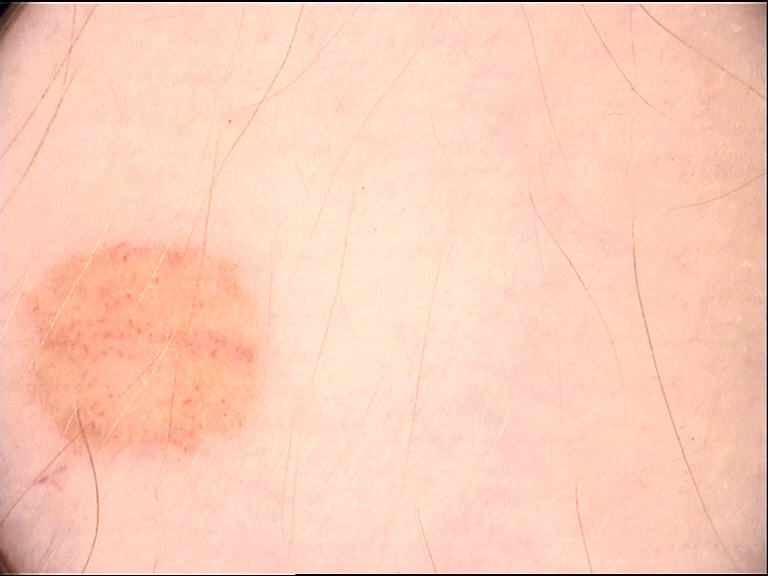image: dermoscopy
lesion_type:
  main_class: banal
  pattern: compound
diagnosis:
  name: compound nevus
  code: cb
  malignancy: benign
  super_class: melanocytic
  confirmation: expert consensus